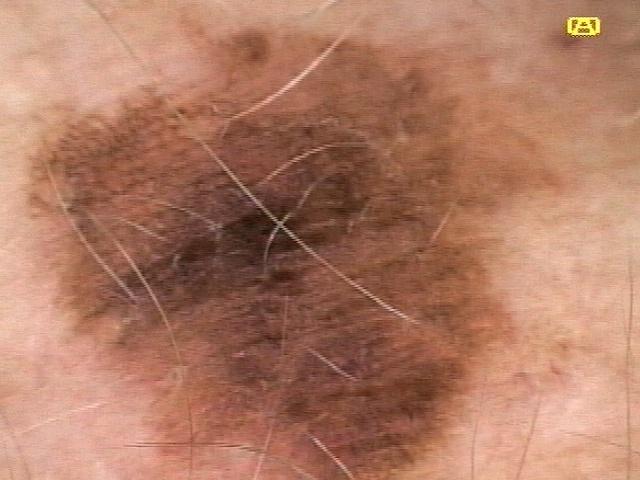Clinical context:
A female subject in their mid-50s. Contact-polarized dermoscopy of a skin lesion. The patient was assessed as Fitzpatrick phototype II. The lesion involves the trunk.
Conclusion:
The biopsy diagnosis was a nevus.